The photograph was taken at an angle:
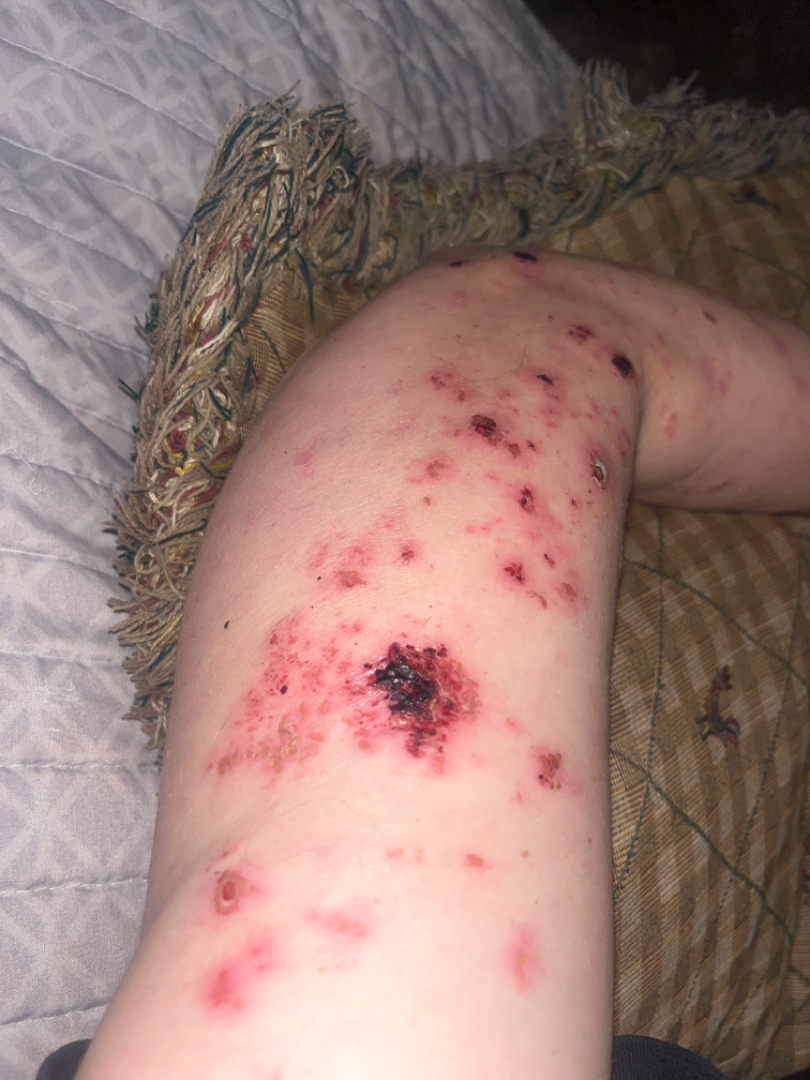The reviewing clinician's impression was: Infected eczema (33%); Herpes Zoster (33%); Leukocytoclastic Vasculitis (33%).